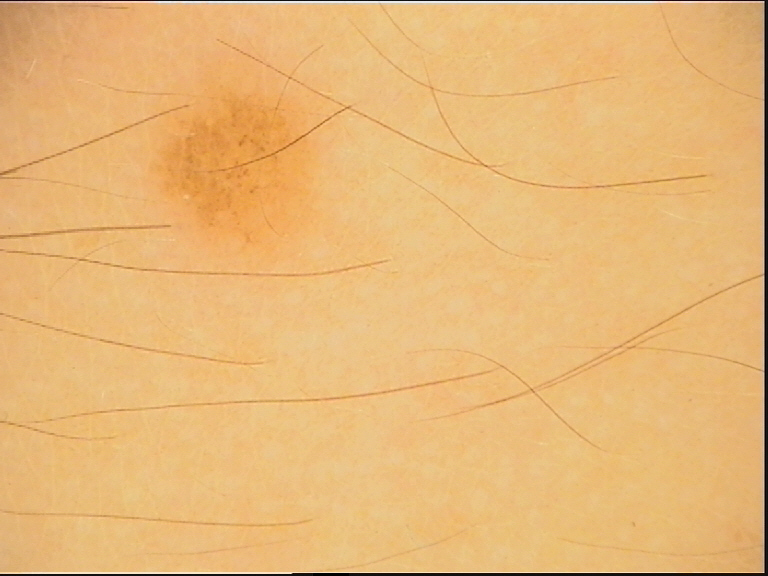Conclusion: Consistent with a dysplastic junctional nevus.